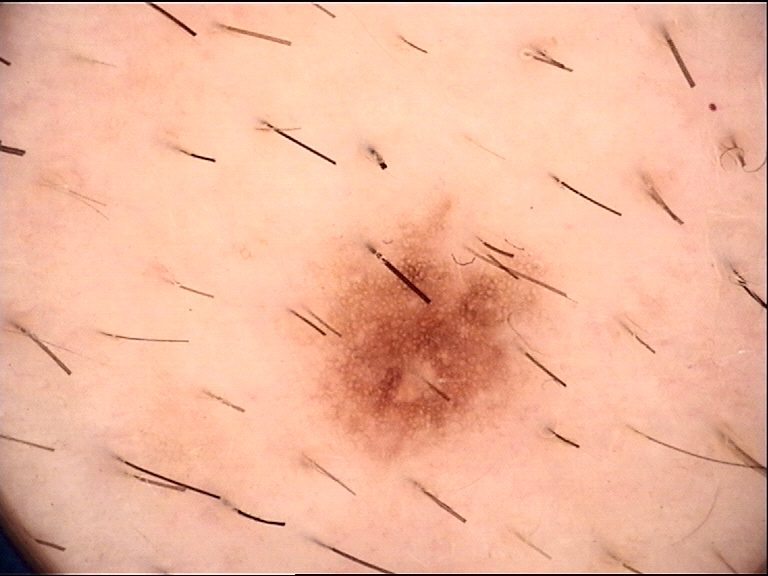diagnostic label=dysplastic junctional nevus (expert consensus).